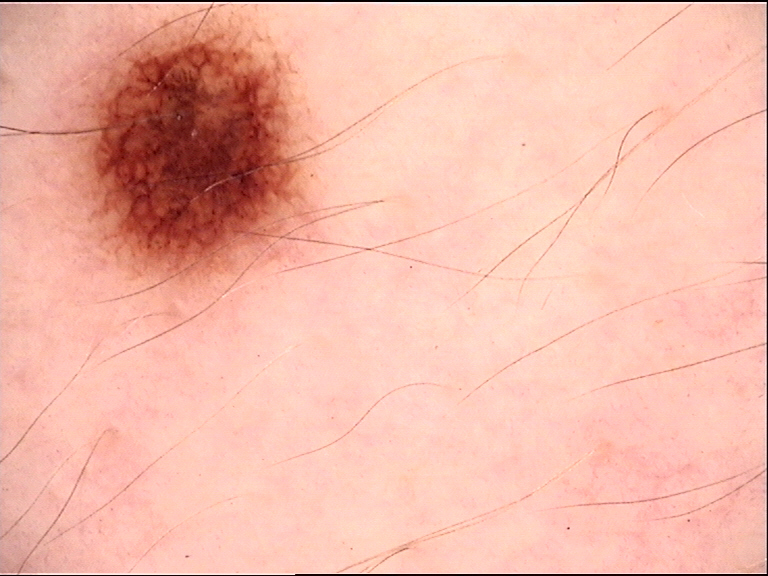Findings:
- image — dermoscopy
- diagnostic label — dysplastic junctional nevus (expert consensus)